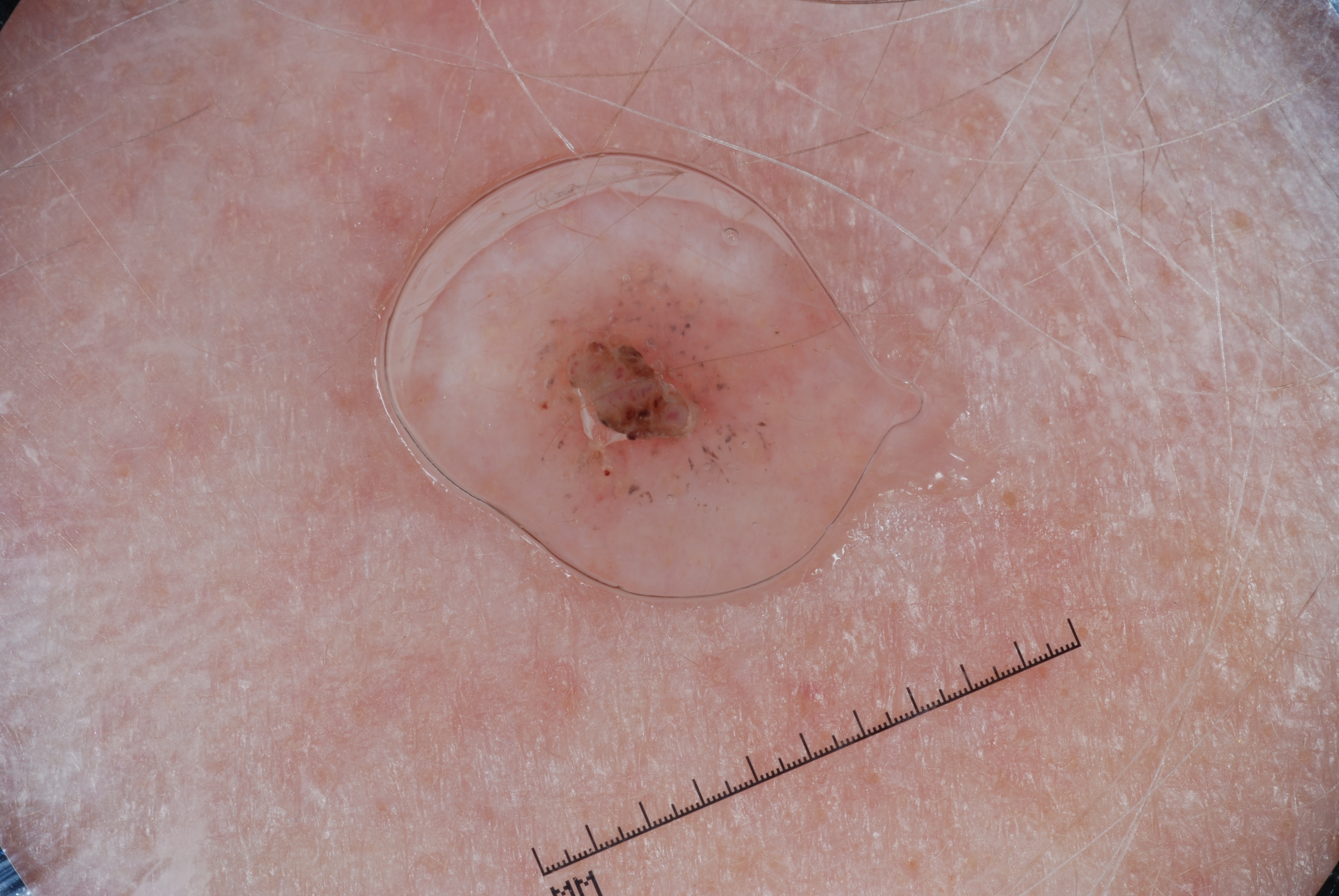Image and clinical context:
A dermoscopic view of a skin lesion. A female subject, aged 73 to 77. As (left, top, right, bottom), the visible lesion spans bbox=[514, 243, 812, 544]. Dermoscopy demonstrates milia-like cysts.
Conclusion:
Expert review diagnosed this as a seborrheic keratosis, a benign lesion.